A dermoscopic photograph of a skin lesion.
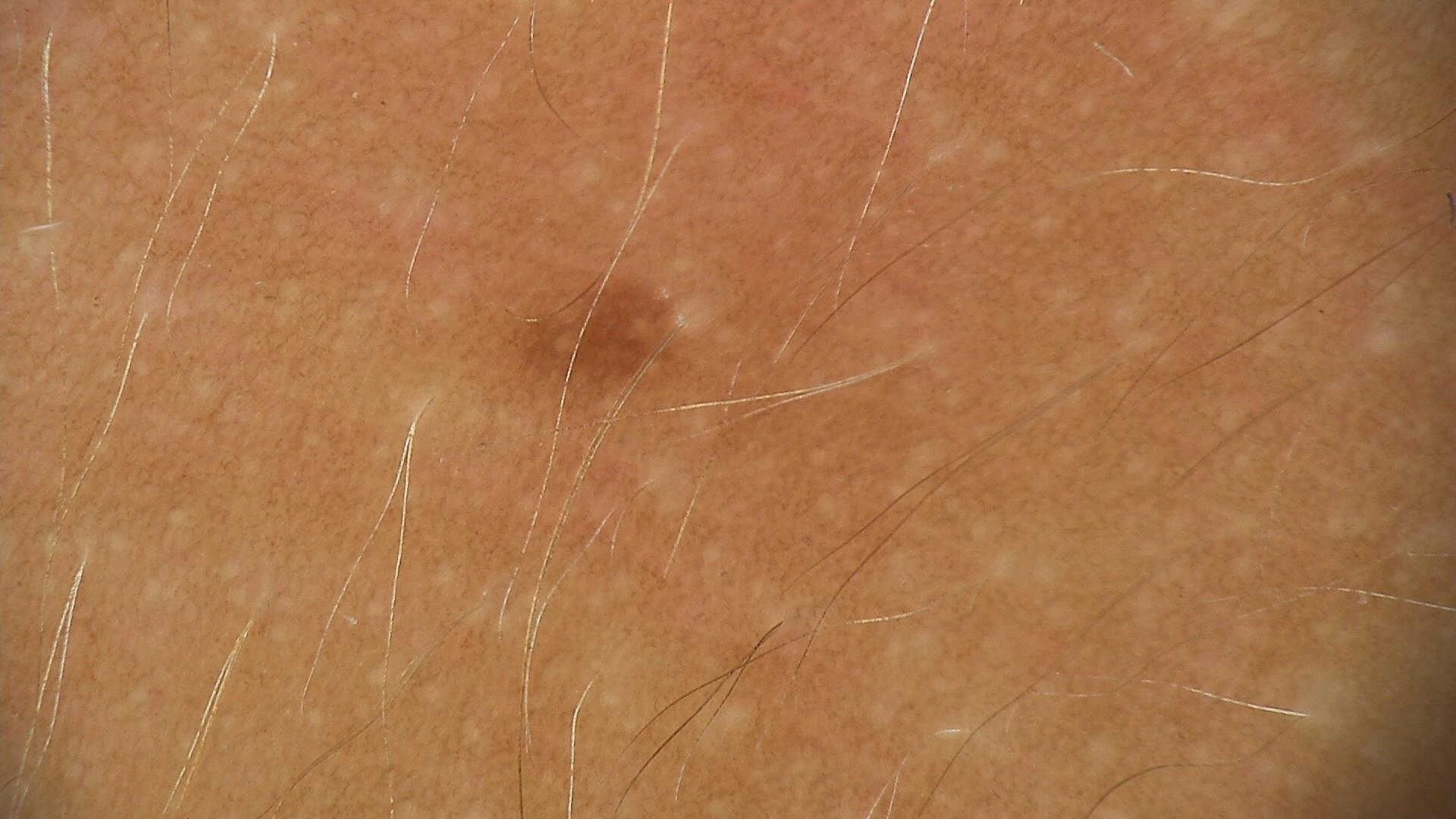Q: How is the lesion classified?
A: banal
Q: What is the diagnosis?
A: junctional nevus (expert consensus)